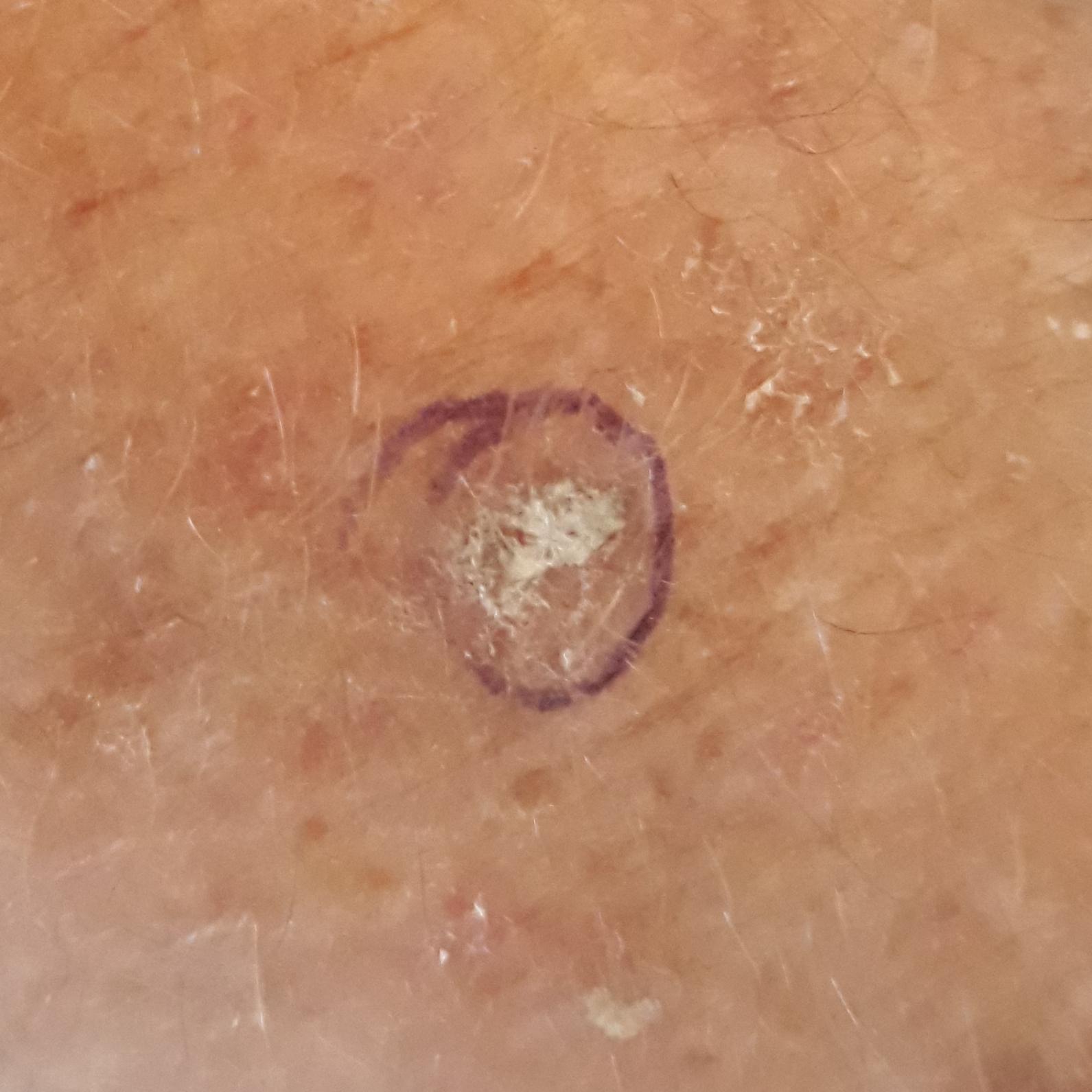| field | value |
|---|---|
| patient | 66 years of age |
| region | a forearm |
| symptoms | elevation, itching |
| assessment | actinic keratosis (clinical consensus) |